A dermoscopic photograph of a skin lesion:
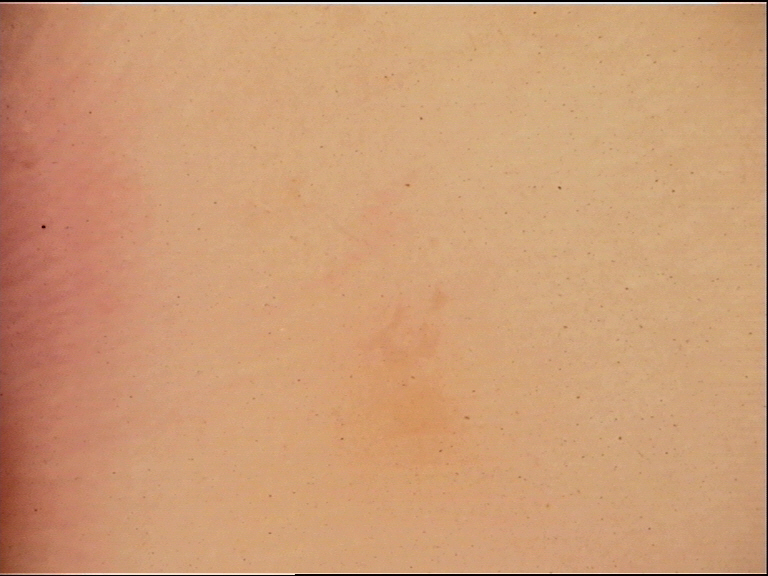Consistent with a banal lesion — an acral junctional nevus.